The lesion is described as rough or flaky, raised or bumpy and fluid-filled. The arm is involved. The condition has been present for one to four weeks. The photo was captured at an angle. The subject is 30–39, female. Self-categorized by the patient as a rash. Fitzpatrick phototype II; lay graders estimated a Monk Skin Tone of 2: 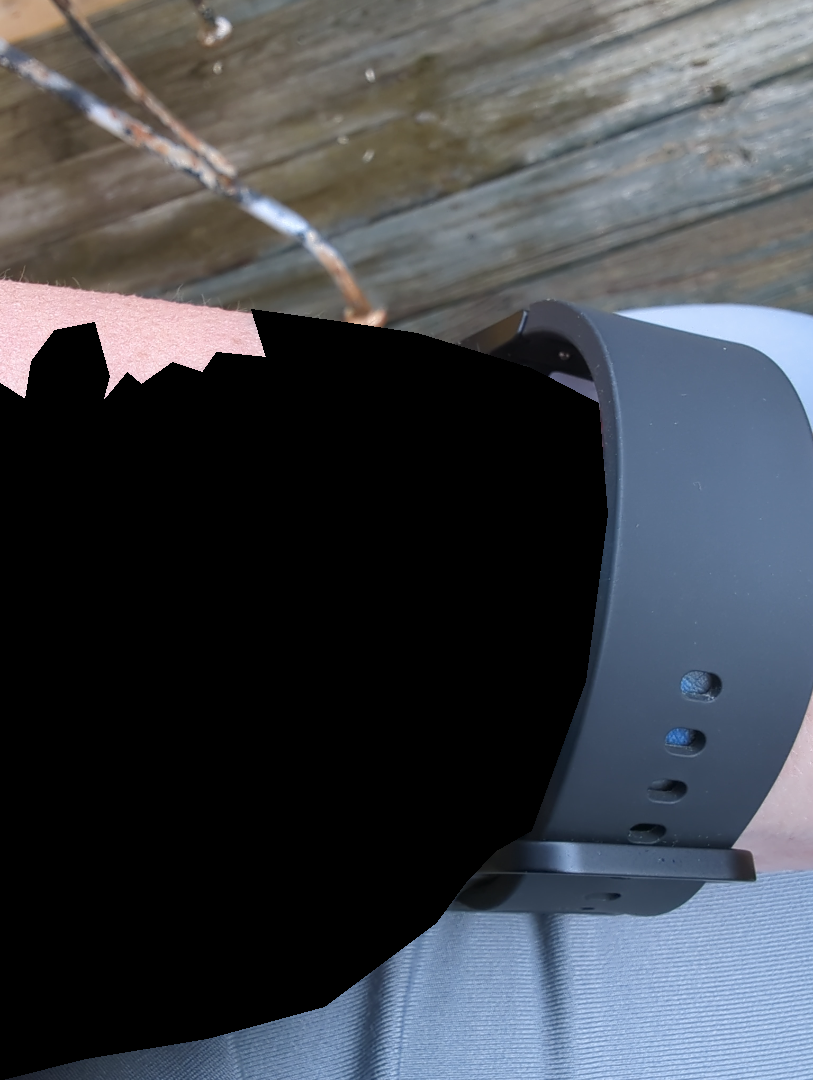Diagnostic features were not clearly distinguishable in this photograph.